A dermatoscopic image of a skin lesion:
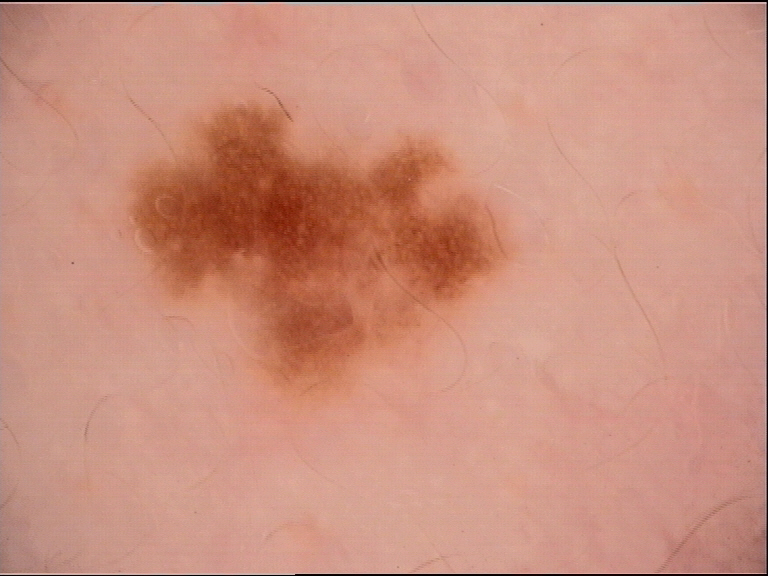The diagnosis was a benign lesion — a dysplastic junctional nevus.